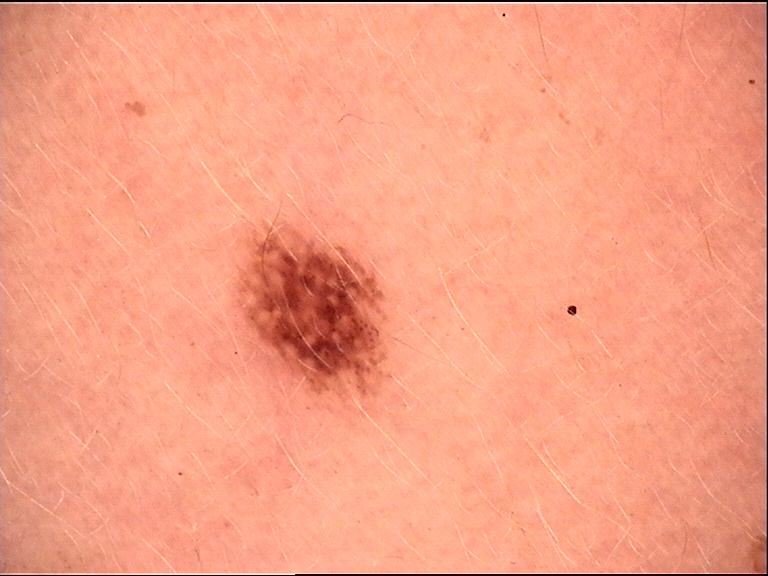Findings: A skin lesion imaged with a dermatoscope. The morphology is that of a compound, banal lesion. Conclusion: The diagnostic label was a Miescher nevus.